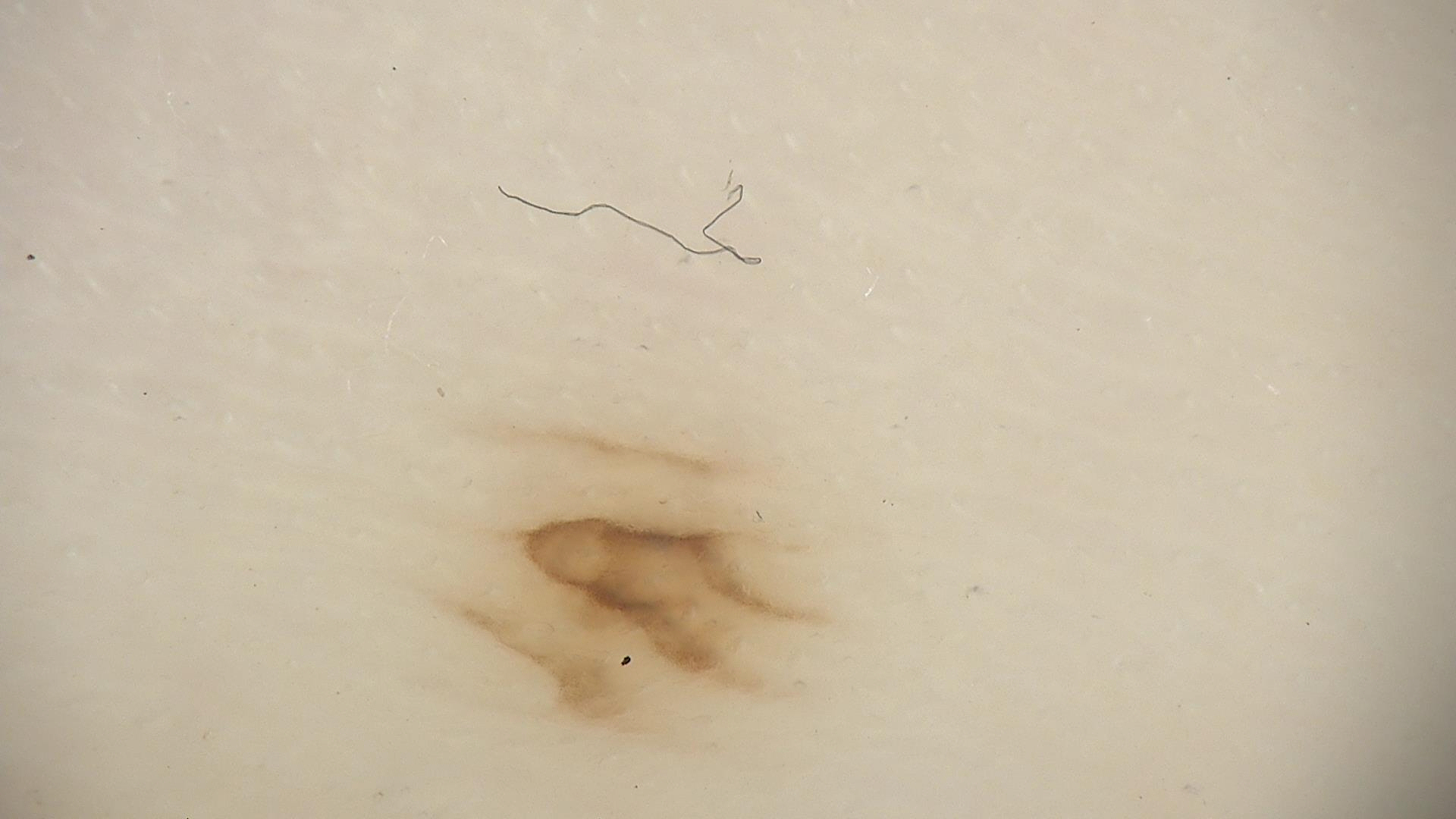<case>
<diagnosis>
<name>acral dysplastic junctional nevus</name>
<code>ajd</code>
<malignancy>benign</malignancy>
<super_class>melanocytic</super_class>
<confirmation>expert consensus</confirmation>
</diagnosis>
</case>